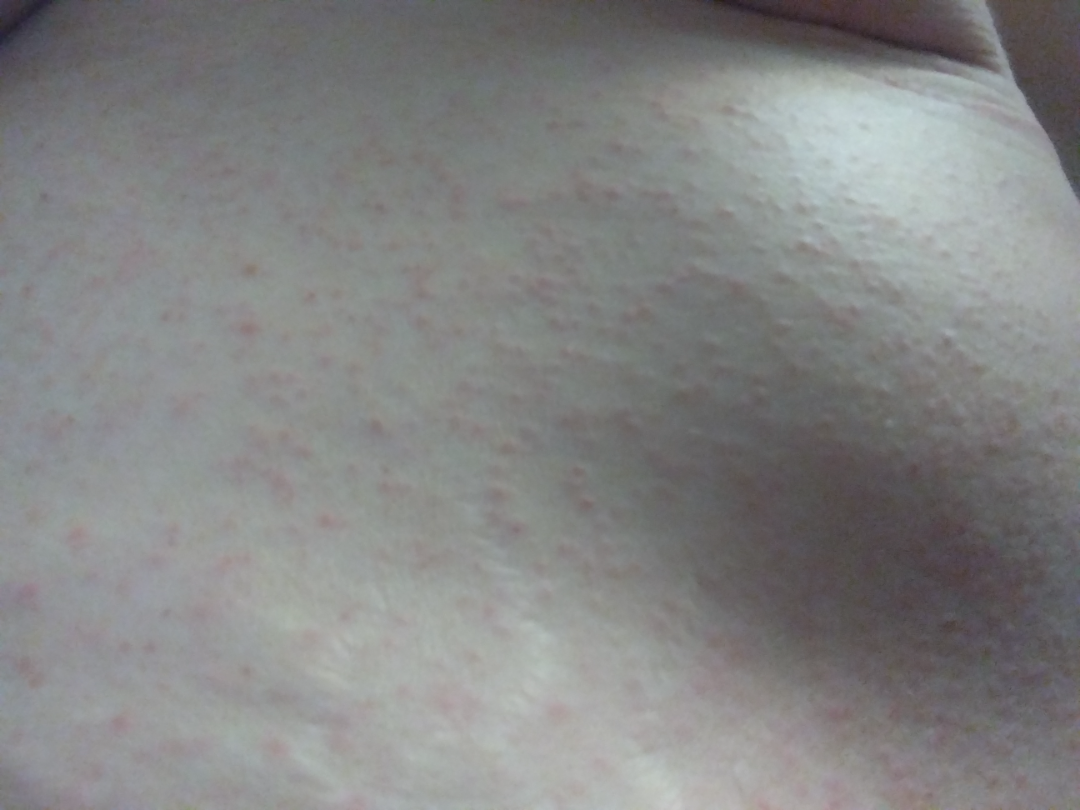{"patient_category": "a rash", "patient": "female, age 40–49", "systemic_symptoms": "none reported", "symptoms": "itching", "shot_type": "at an angle", "texture": "raised or bumpy", "duration": "about one day", "body_site": ["back of the torso", "front of the torso"], "differential": {"tied_lead": ["Drug Rash", "Viral Exanthem", "Hypersensitivity"]}}